The affected area is the head or neck and arm, an image taken at a distance: 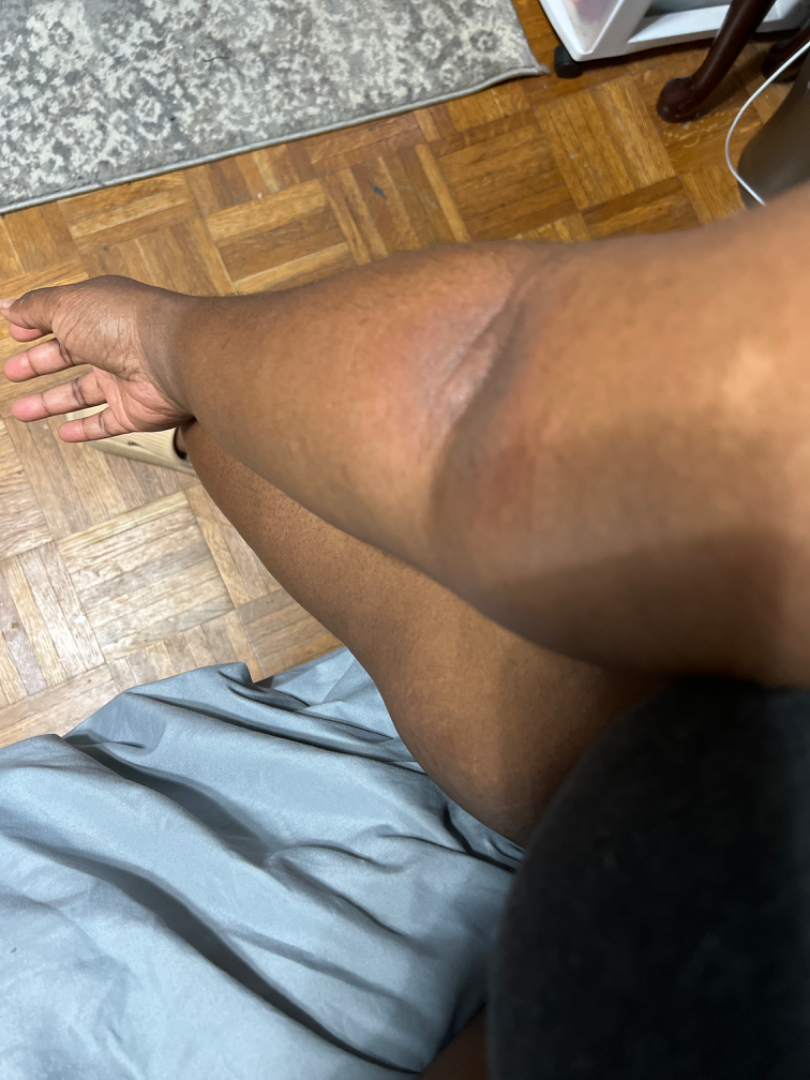Single-reviewer assessment: the reviewer's impression was Eczema.